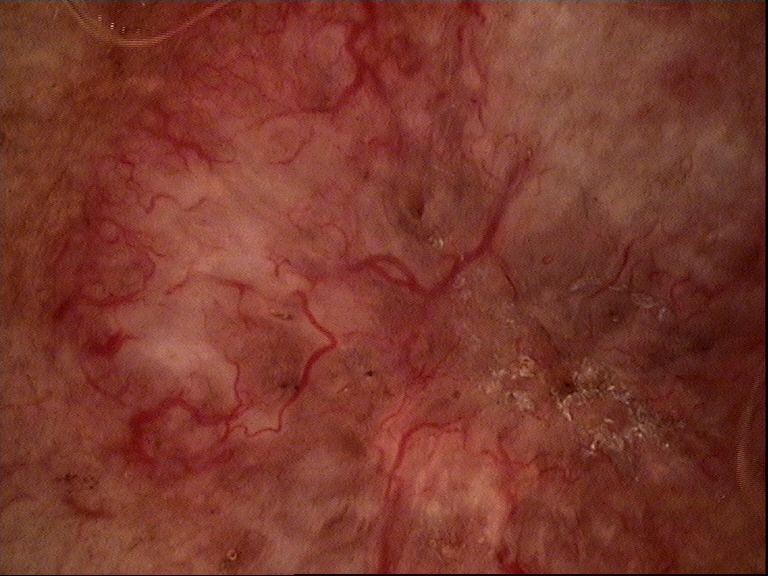A skin lesion imaged with a dermatoscope.
Histopathology confirmed a keratinocytic lesion — a basal cell carcinoma.